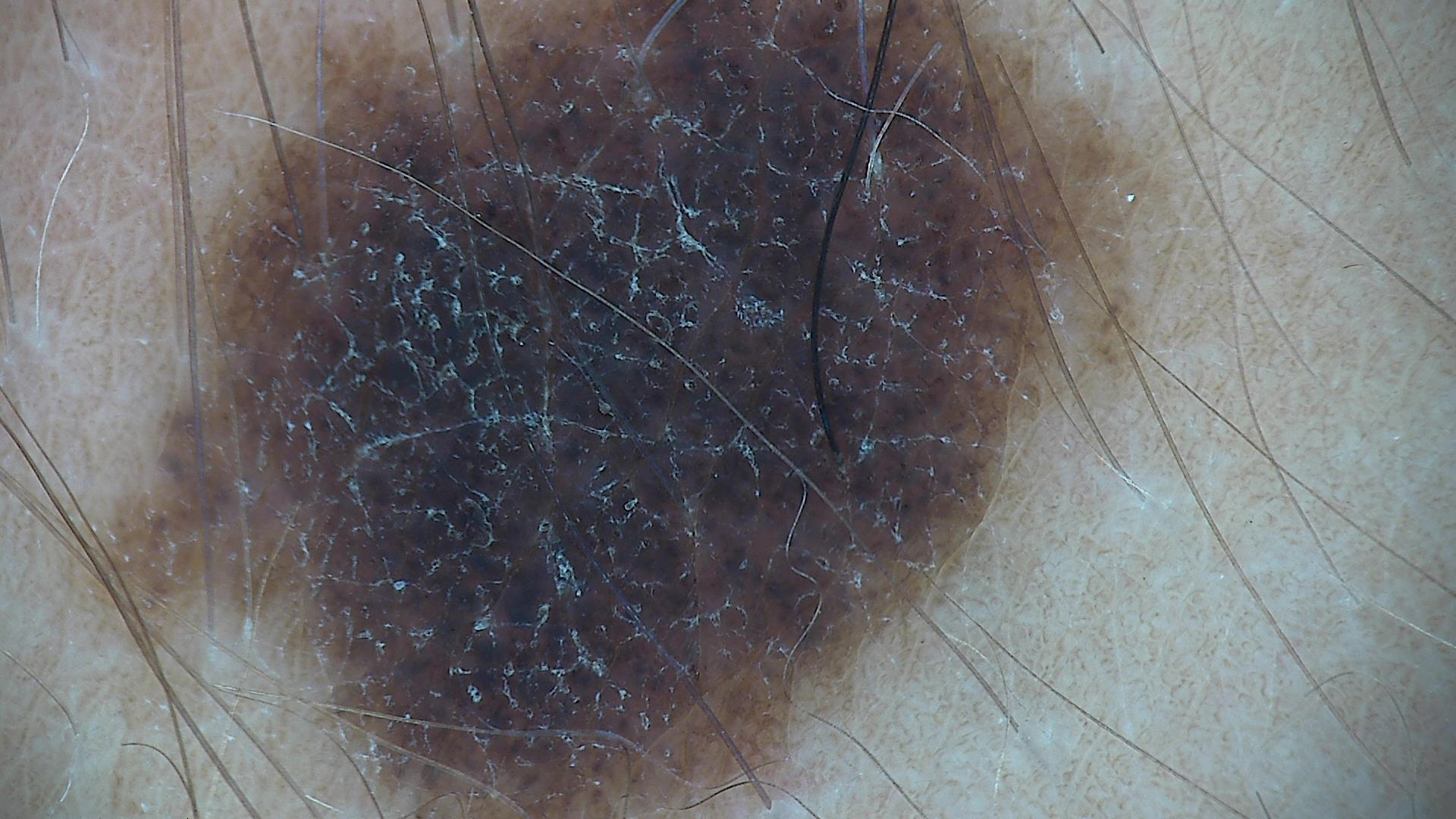The diagnostic label was a congenital compound nevus.